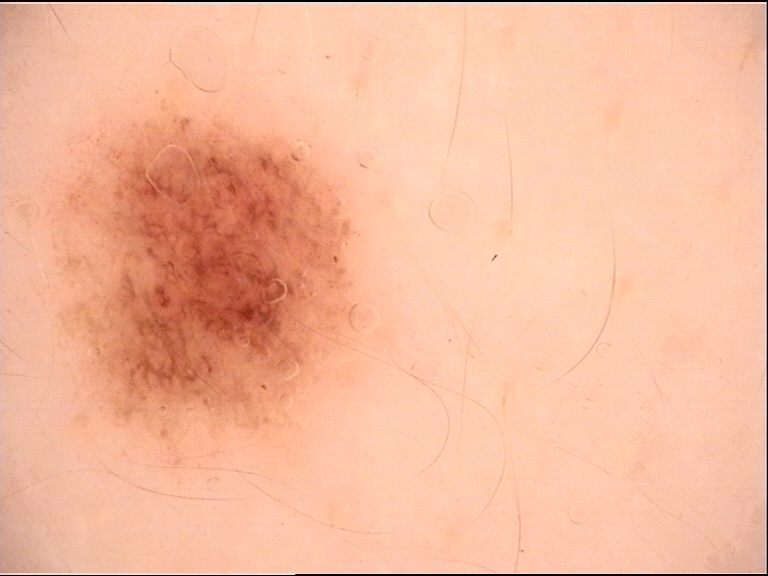A dermoscopic close-up of a skin lesion. Diagnosed as a dysplastic junctional nevus.